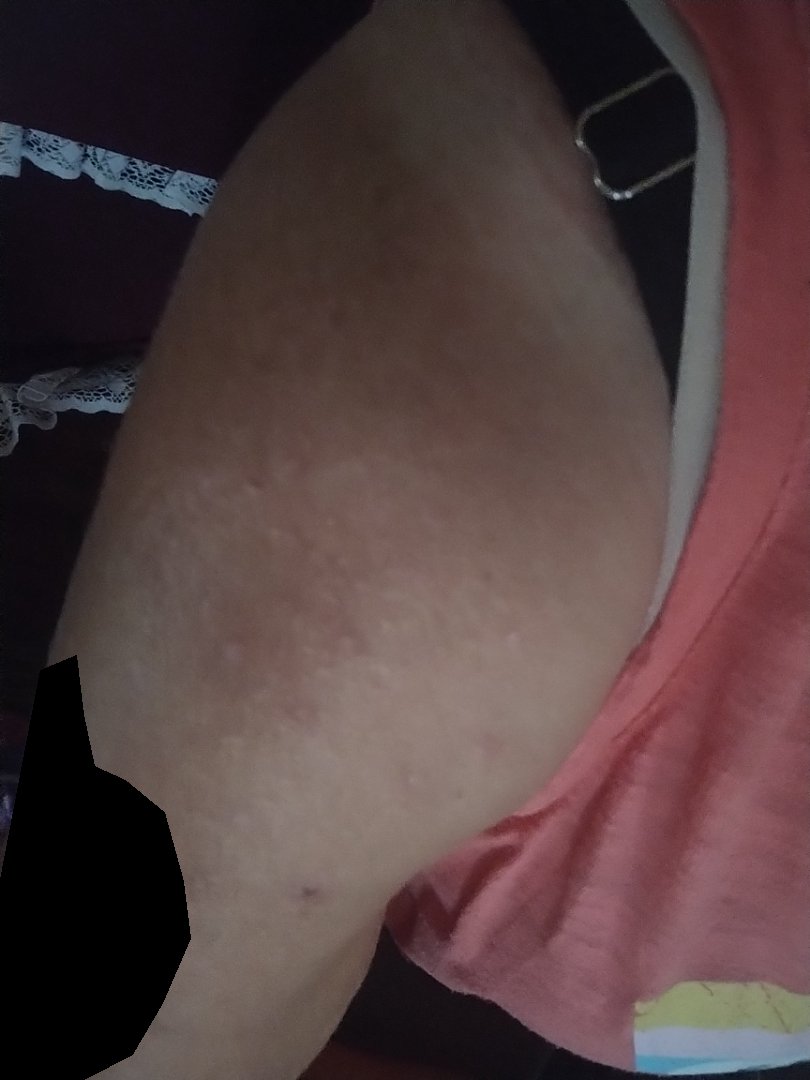framing: close-up | patient's own categorization: a rash | symptoms: darkening, pain, burning and itching | lesion texture: raised or bumpy, fluid-filled and flat | location: arm | differential diagnosis: most consistent with Folliculitis; also consider Eczema.